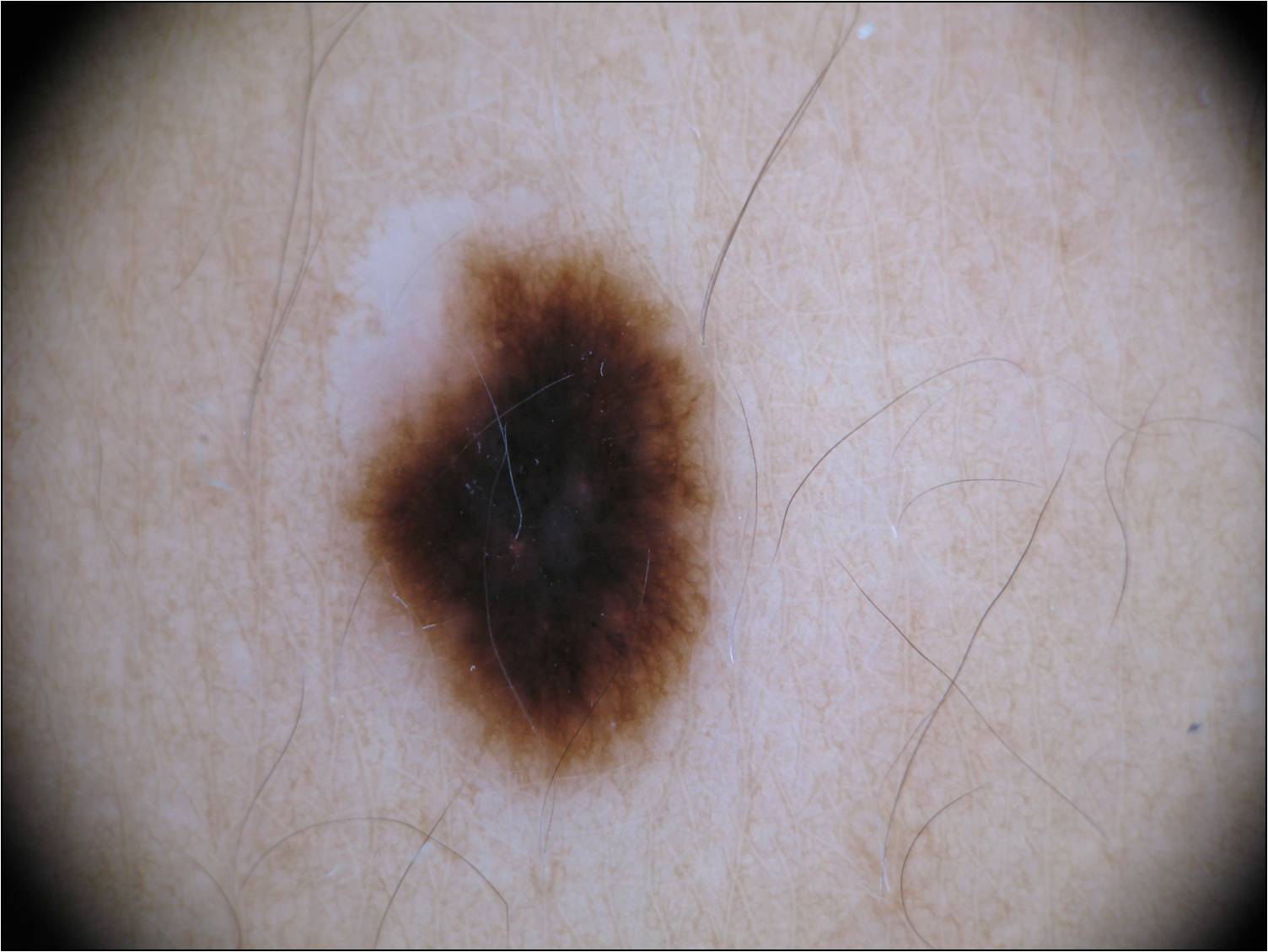Findings: A dermoscopic view of a skin lesion. A female patient, about 50 years old. As (left, top, right, bottom), the lesion is bounded by [326,242,717,793]. Dermoscopic examination shows pigment network; no milia-like cysts, negative network, streaks, or globules. Conclusion: The diagnostic assessment was a melanocytic nevus, a benign skin lesion.